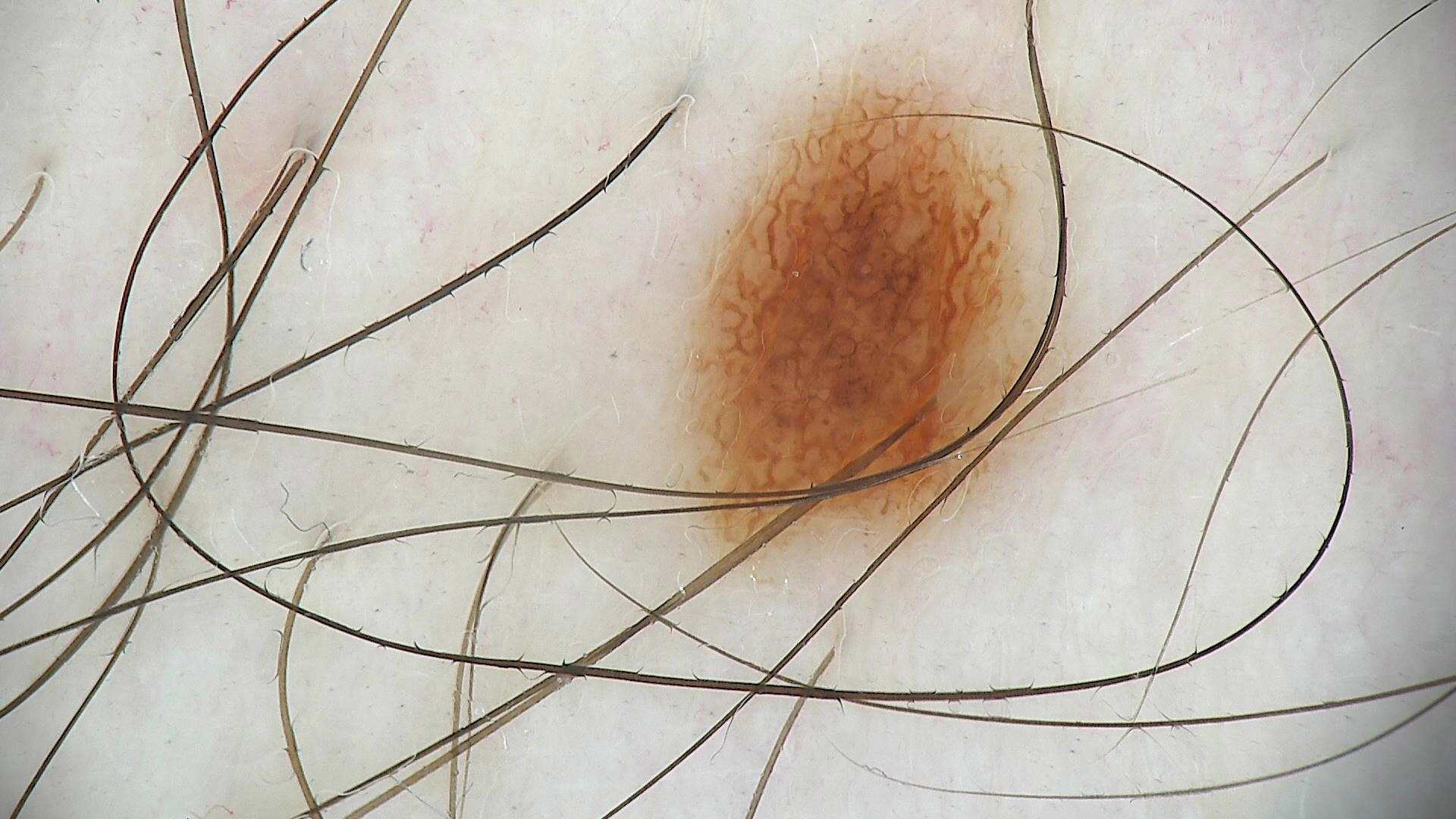<lesion>
<image>dermoscopy</image>
<diagnosis>
<name>junctional nevus</name>
<code>jb</code>
<malignancy>benign</malignancy>
<super_class>melanocytic</super_class>
<confirmation>expert consensus</confirmation>
</diagnosis>
</lesion>